A dermoscopic view of a skin lesion · a male patient, aged 43-47:
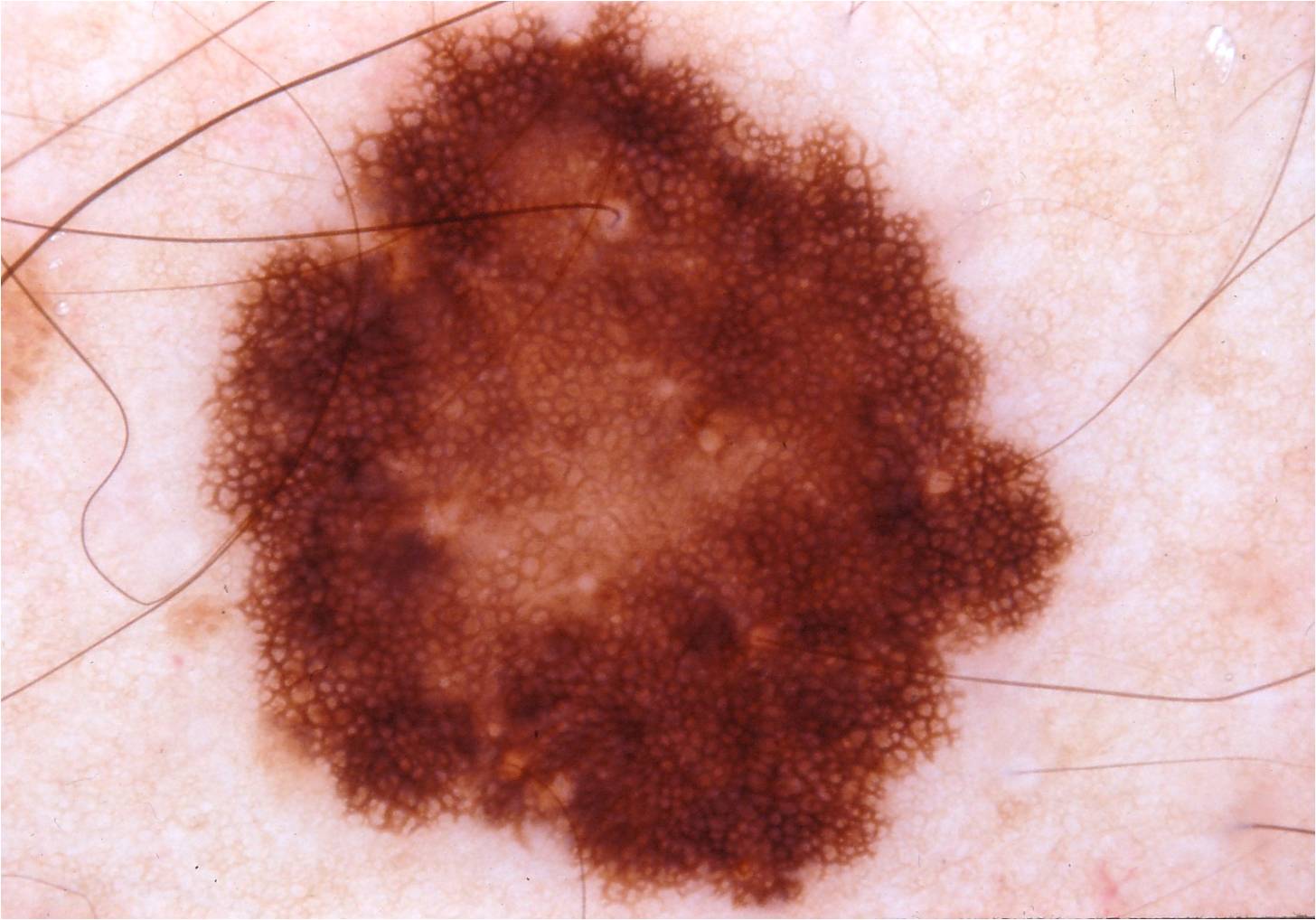Image and clinical context:
The lesion is bounded by 190/0/1092/915. Dermoscopic assessment notes pigment network.
Assessment:
Clinically diagnosed as a melanocytic nevus.